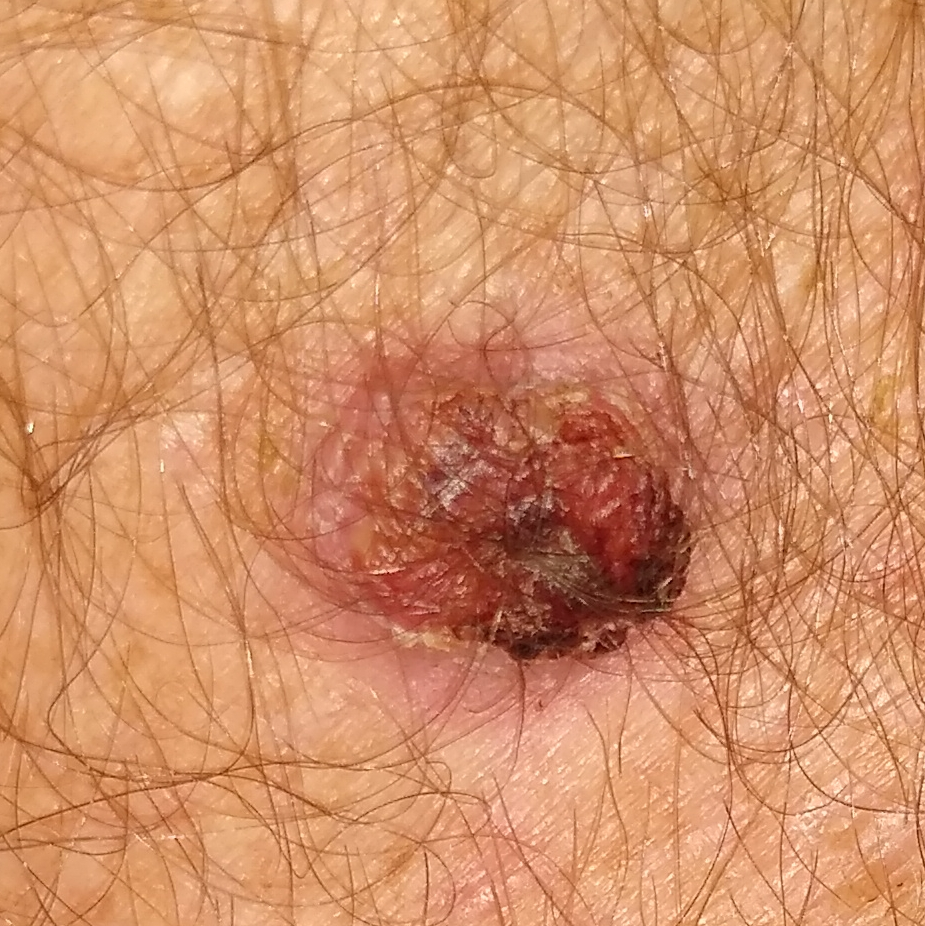A male patient in their 50s. A clinical photo of a skin lesion taken with a smartphone. The lesion is on an arm. The patient describes that the lesion is elevated, itches, hurts, has bled, and has grown. Histopathology confirmed a basal cell carcinoma.